A dermoscopy image of a single skin lesion.
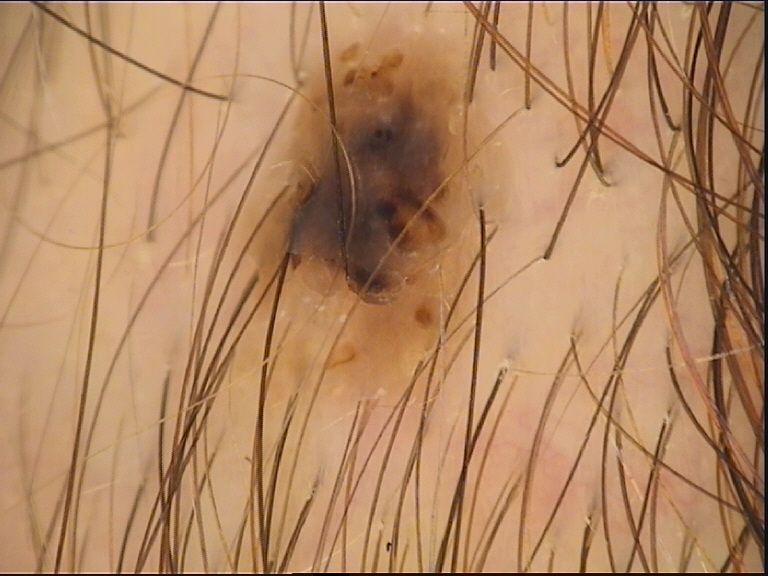Q: What was the diagnostic impression?
A: compound nevus (expert consensus)